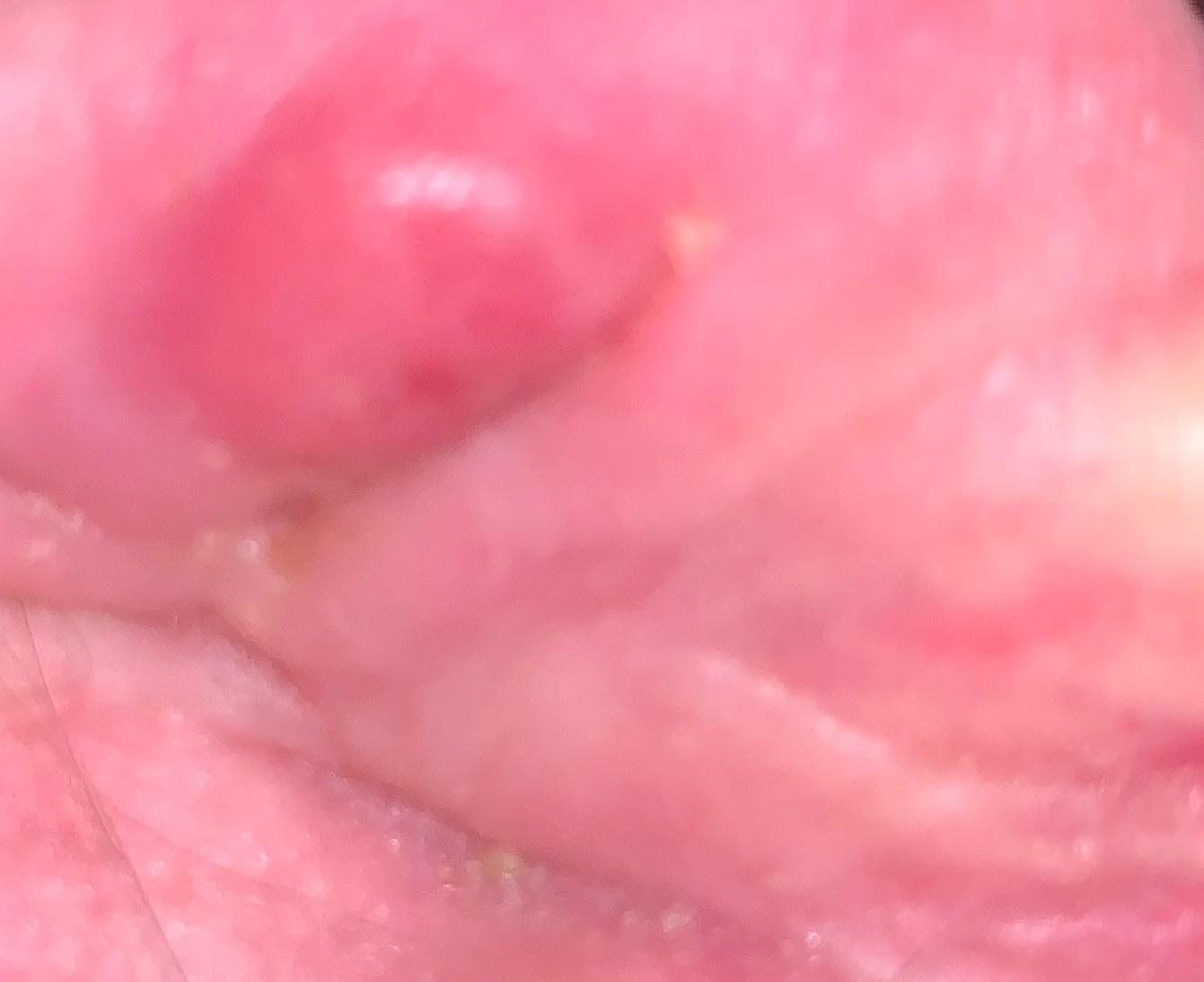Notes:
• Fitzpatrick · II
• patient · female, aged 63-67
• body site · the head or neck
• diagnosis · Squamous cell carcinoma (biopsy-proven)